Located on the front of the torso; the photograph is a close-up of the affected area; male contributor, age 30–39 — 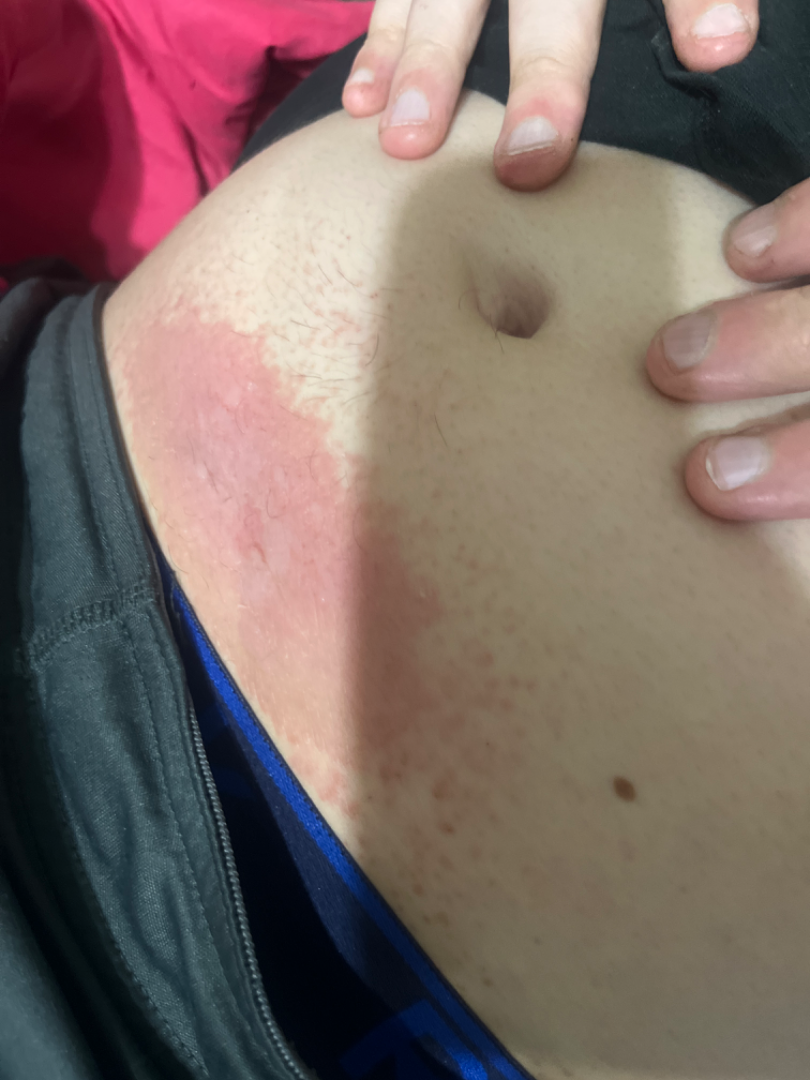Review: Most consistent with Allergic Contact Dermatitis.